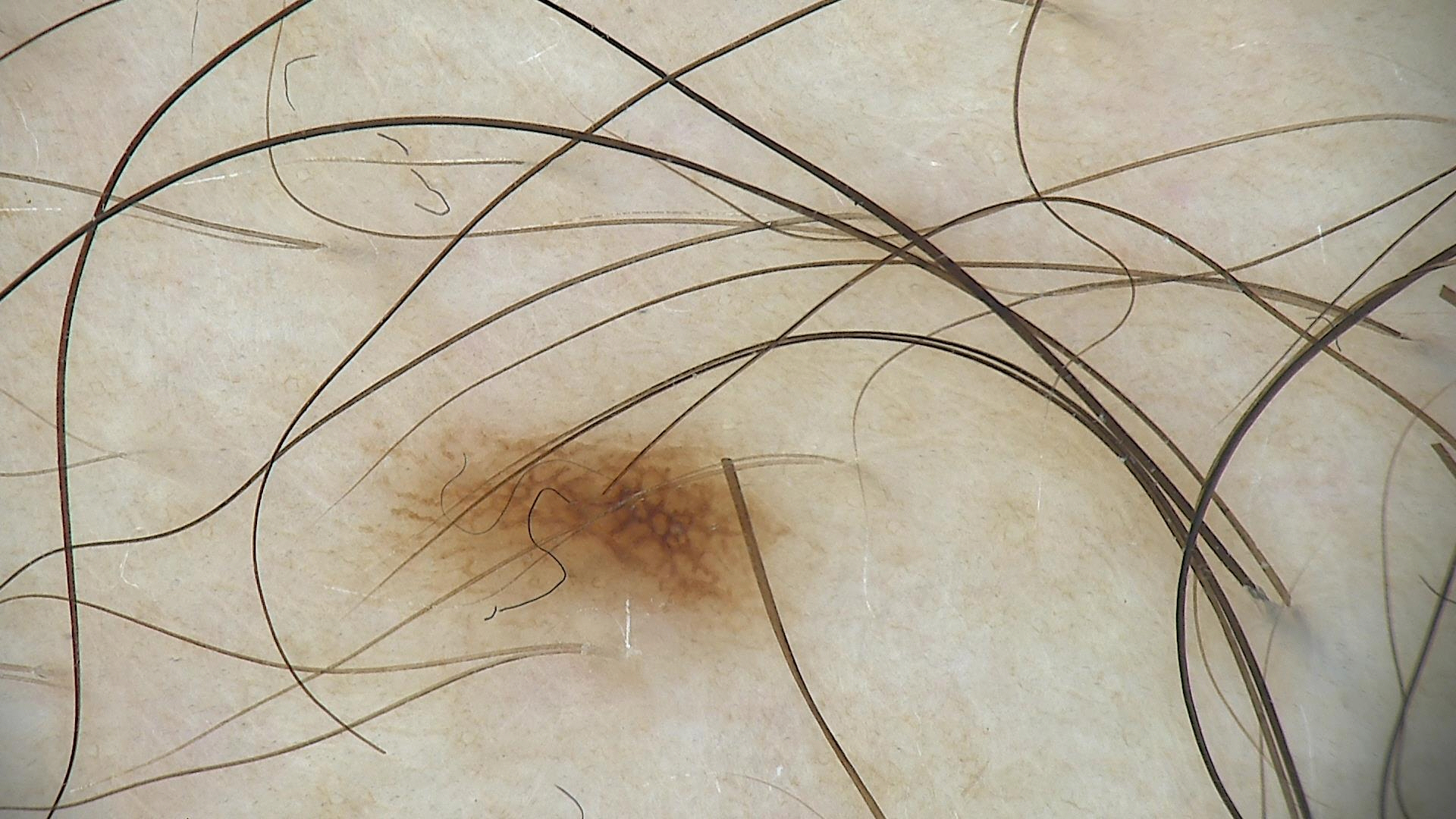Impression:
Diagnosed as a dysplastic junctional nevus.